Dermoscopy of a skin lesion; the patient is female.
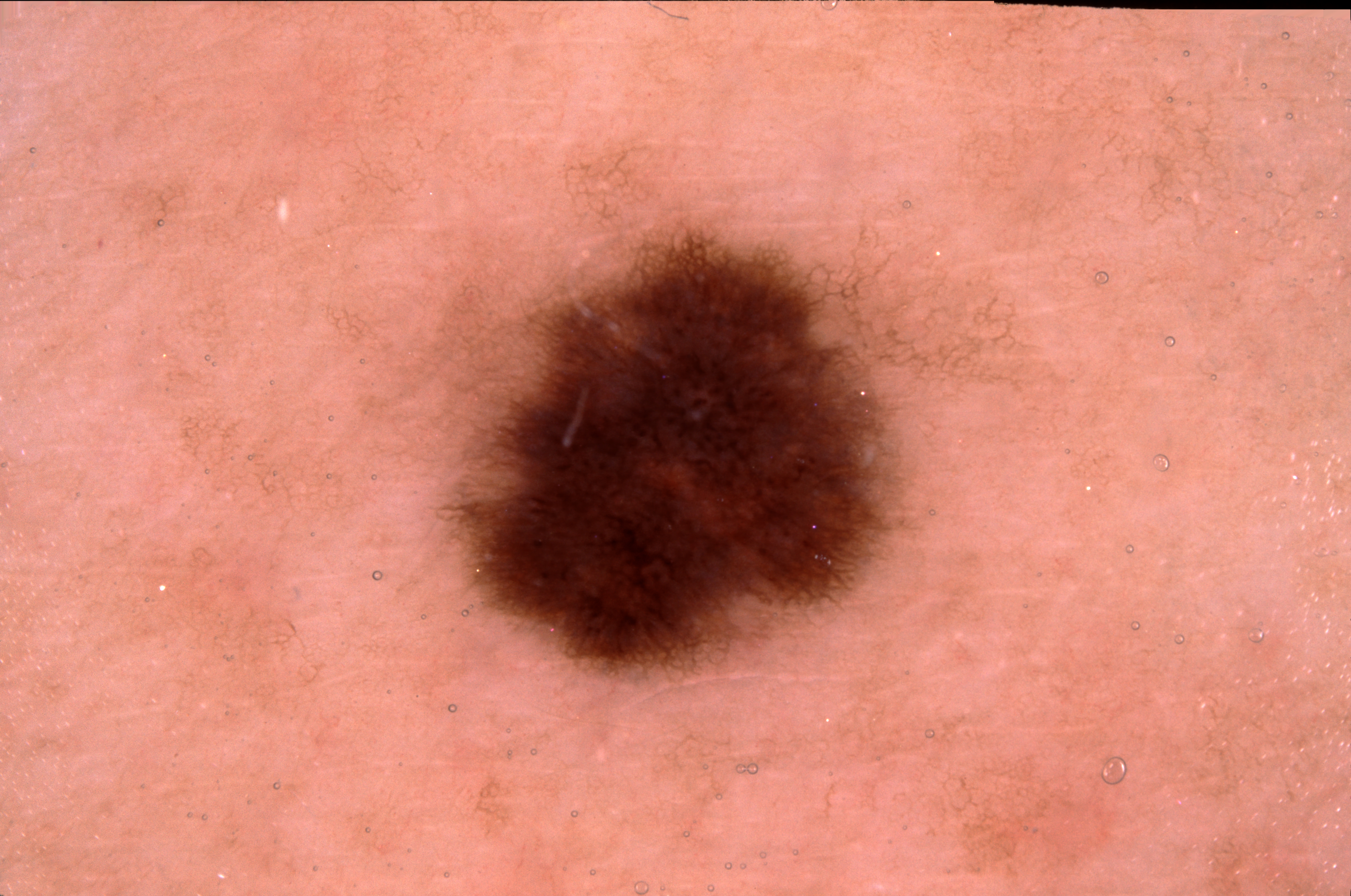{
  "lesion_extent": "moderate",
  "dermoscopic_features": {
    "present": [
      "pigment network"
    ],
    "absent": [
      "streaks",
      "negative network",
      "milia-like cysts"
    ]
  },
  "lesion_location": {
    "bbox_xyxy": [
      465,
      231,
      897,
      672
    ]
  },
  "diagnosis": {
    "name": "melanocytic nevus",
    "malignancy": "benign",
    "lineage": "melanocytic",
    "provenance": "clinical"
  }
}